The patient reported no systemic symptoms. The patient considered this a rash. The photo was captured at a distance. The lesion involves the leg. Reported lesion symptoms include itching and enlargement. Female contributor, age 50–59. The condition has been present for less than one week — 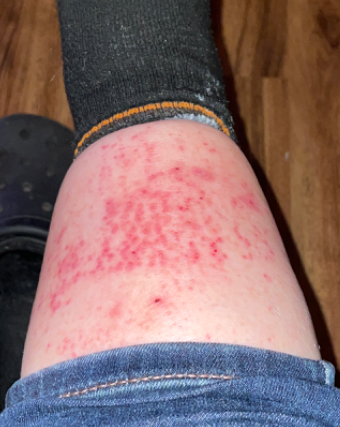On remote review of the image, the leading impression is Eczema.